No associated systemic symptoms reported · symptoms reported: burning and itching · texture is reported as flat, raised or bumpy and rough or flaky · the arm is involved · the photograph is a close-up of the affected area — 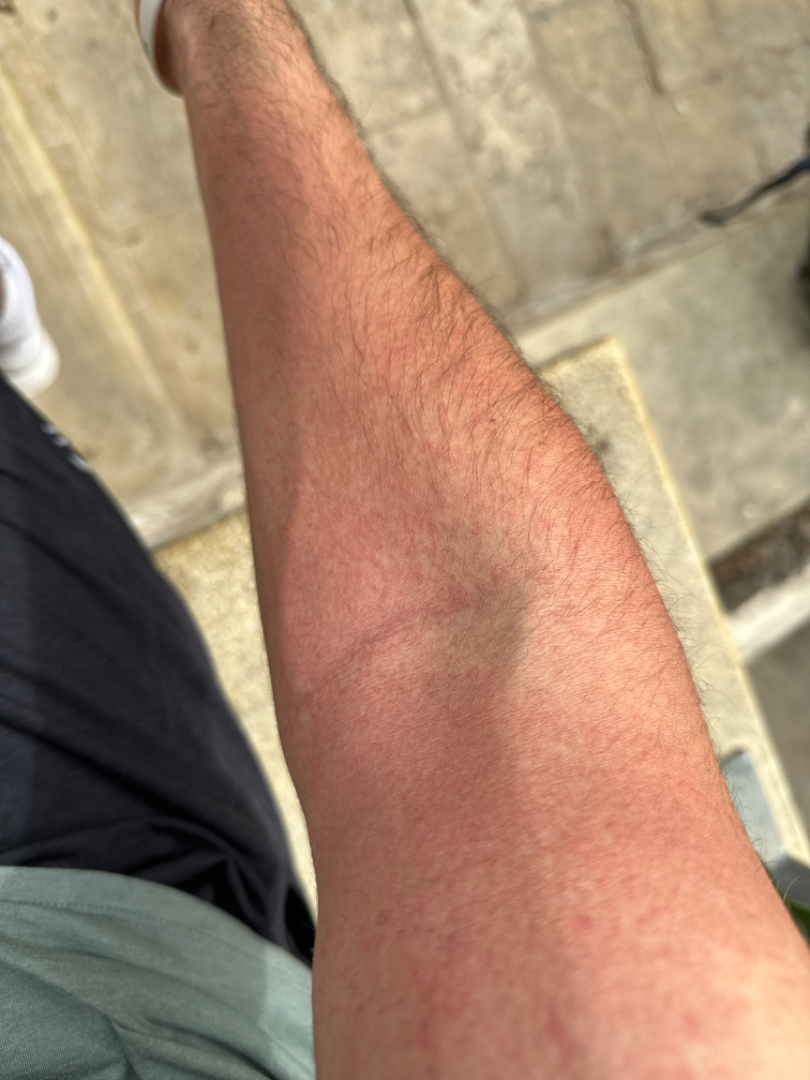Reviewed remotely by three dermatologists: the impression was split between Drug Rash and Acute dermatitis, NOS; a remote consideration is Viral Exanthem; less probable is Allergic Contact Dermatitis; less likely is Eczema.